Imaged for a research study, with no referral diagnosis recorded. Dermoscopy of a skin lesion. A female patient age 59. The patient says their skin reddens with sun exposure. A moderate number of moles by the patient's own estimate:
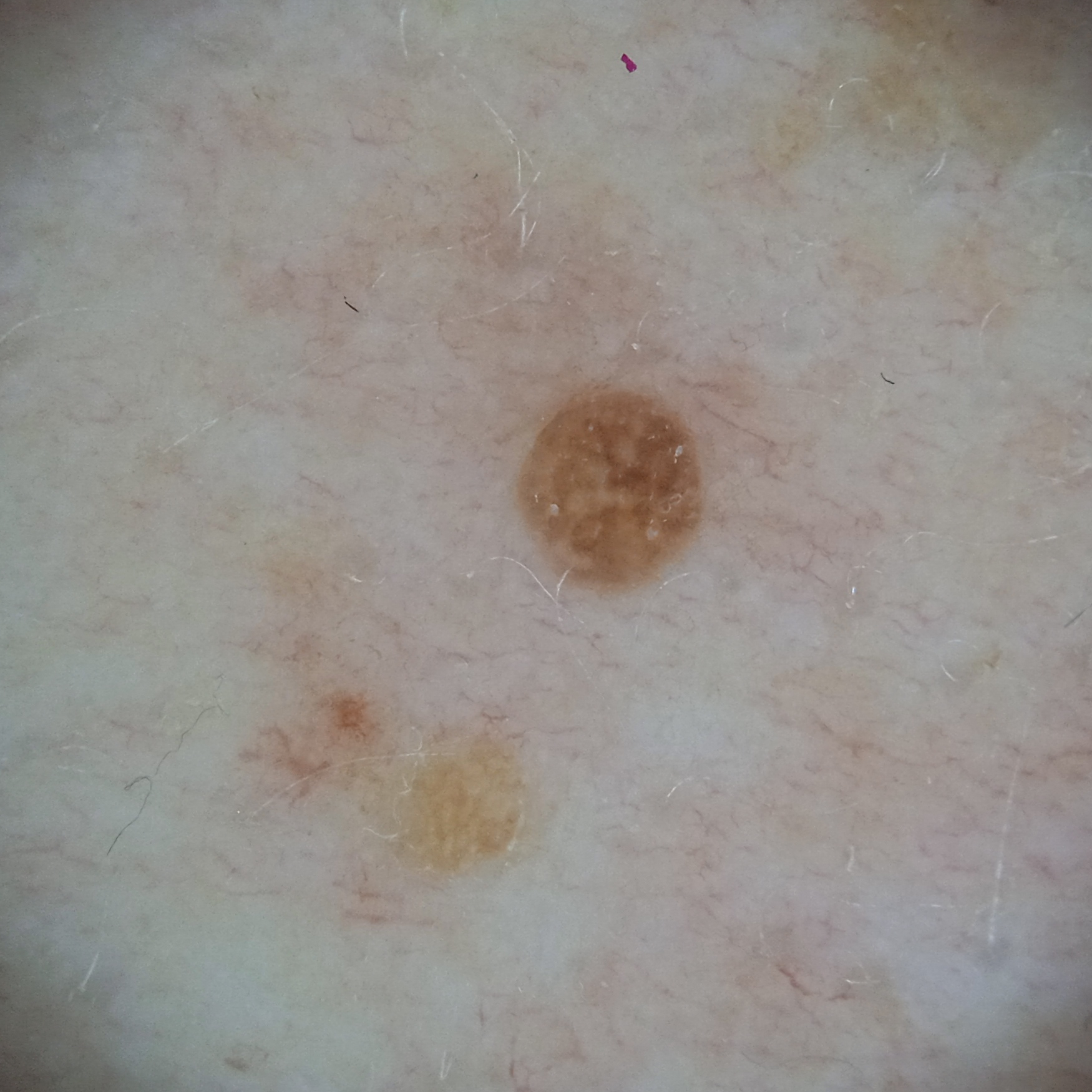  lesion_location: the torso
  lesion_size:
    diameter_mm: 2.2
  diagnosis:
    name: seborrheic keratosis
    malignancy: benign